Close-up view. The subject is a male aged 18–29: 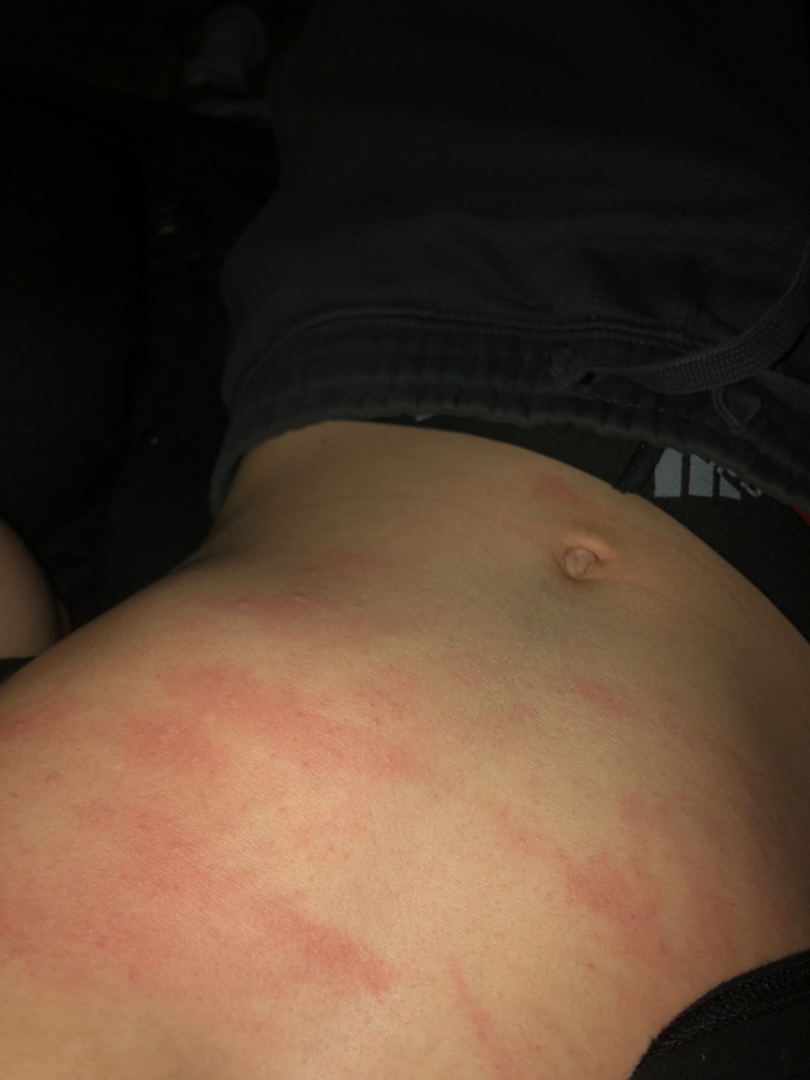Review: On remote review of the image, Urticaria (favored).